A close-up photograph · located on the arm.
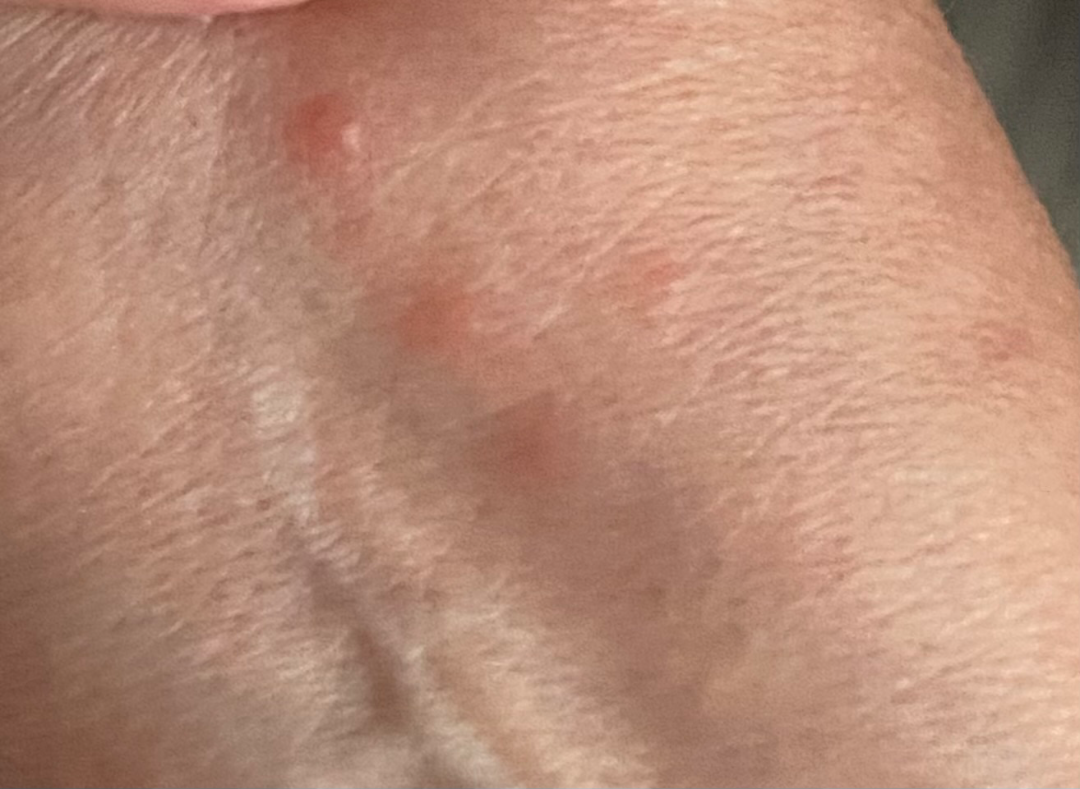lesion symptoms=burning and itching | systemic symptoms=none reported | texture=fluid-filled and raised or bumpy | patient's own categorization=a rash | symptom duration=less than one week | diagnostic considerations=favoring Insect Bite; an alternative is Urticaria; also raised was Allergic Contact Dermatitis.